A male patient, aged approximately 70; a dermoscopic image of a skin lesion:
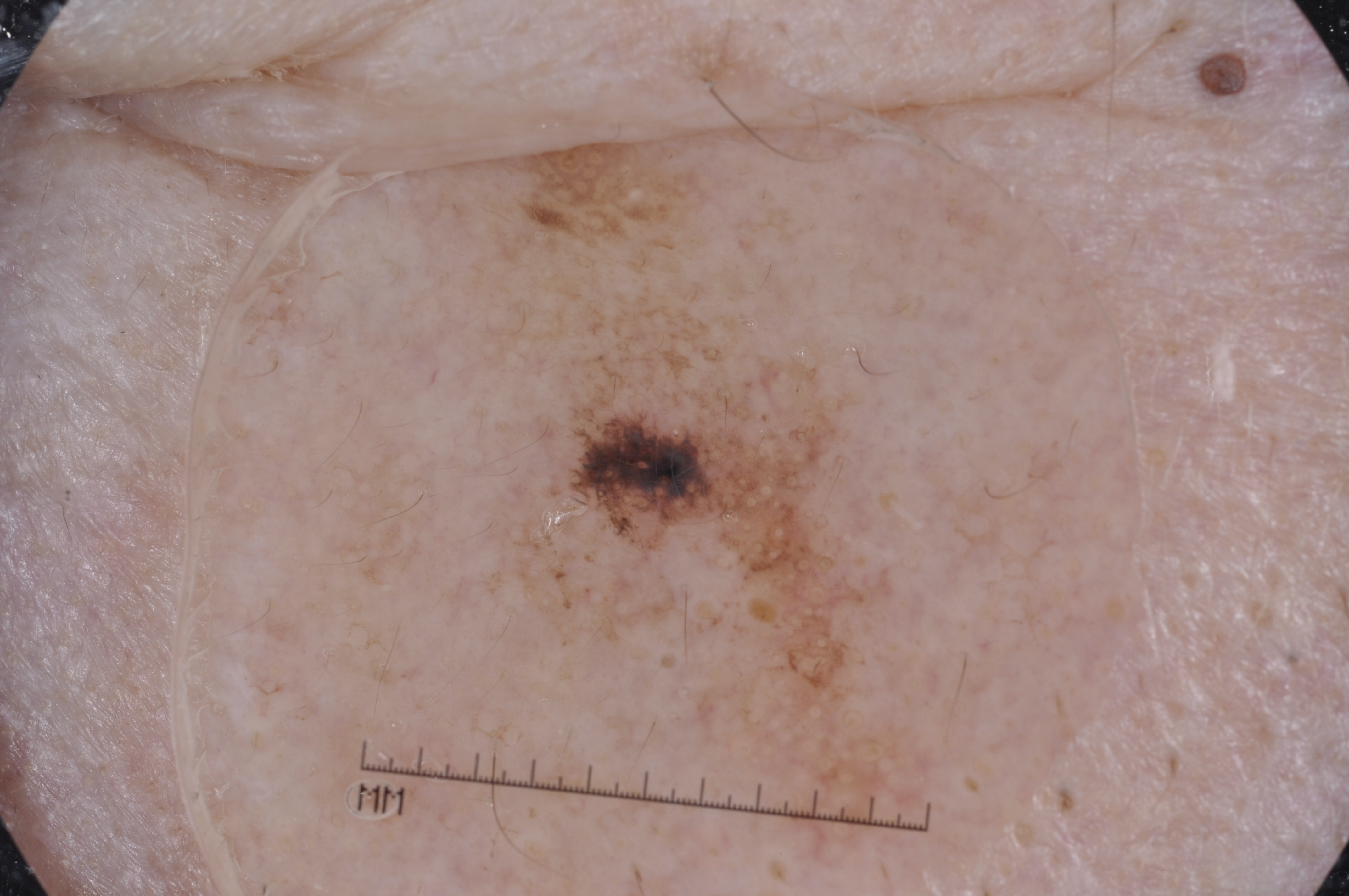Q: How large is the lesion within the image?
A: moderate
Q: What does dermoscopy show?
A: pigment network and milia-like cysts
Q: Where is the lesion in the image?
A: <bbox>430, 130, 906, 806</bbox>
Q: What did the assessment conclude?
A: a melanoma, a malignant lesion